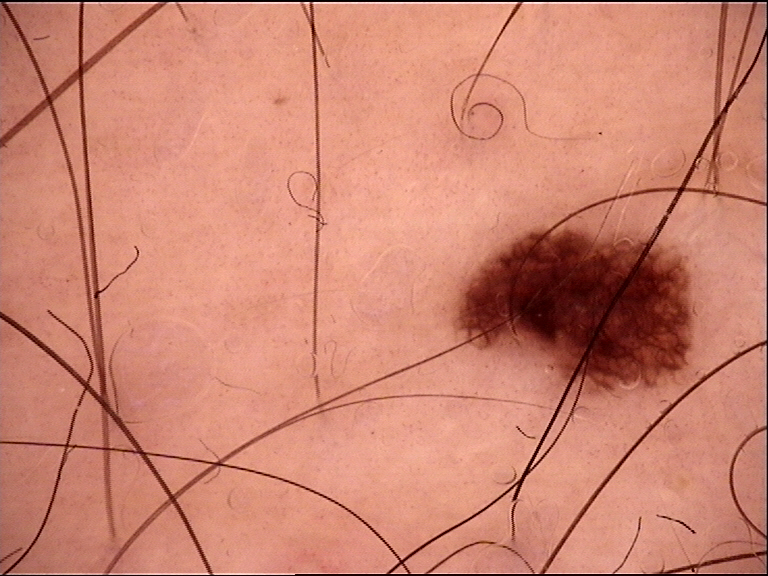<dermoscopy>
  <diagnosis>
    <name>junctional nevus</name>
    <code>jb</code>
    <malignancy>benign</malignancy>
    <super_class>melanocytic</super_class>
    <confirmation>expert consensus</confirmation>
  </diagnosis>
</dermoscopy>